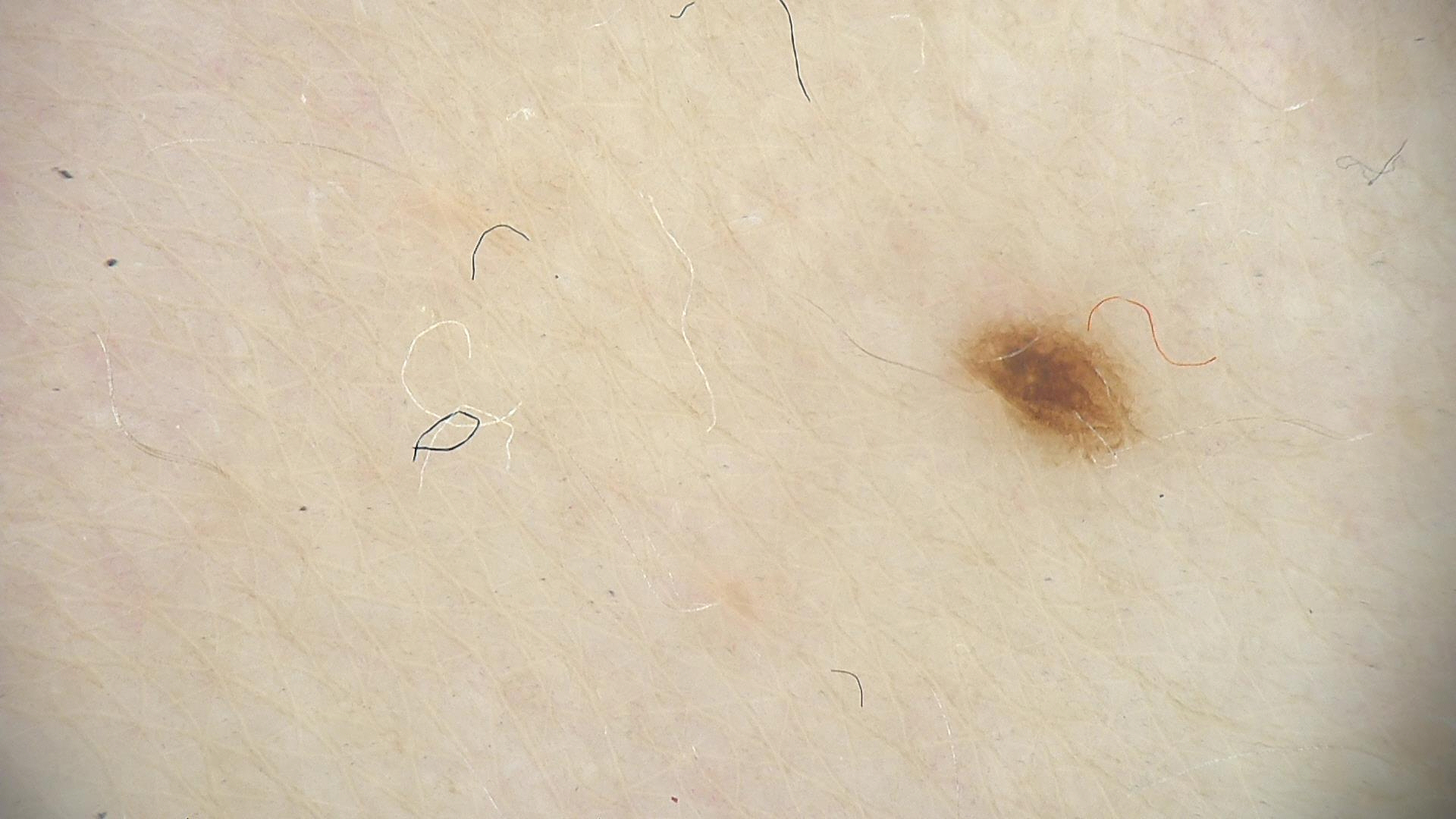{"diagnosis": {"name": "dysplastic junctional nevus", "code": "jd", "malignancy": "benign", "super_class": "melanocytic", "confirmation": "expert consensus"}}